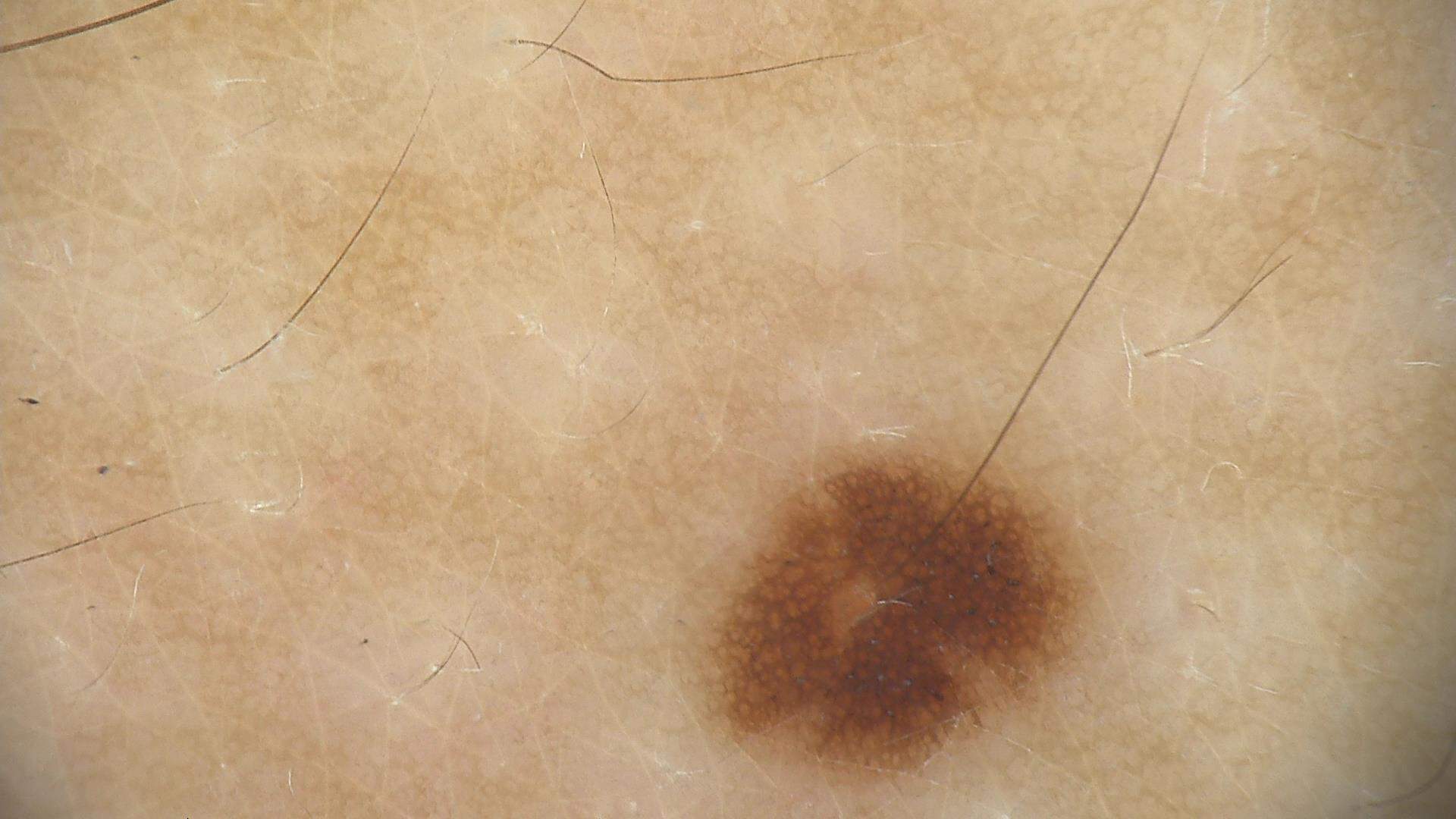<lesion>
<diagnosis>
<name>dysplastic junctional nevus</name>
<code>jd</code>
<malignancy>benign</malignancy>
<super_class>melanocytic</super_class>
<confirmation>expert consensus</confirmation>
</diagnosis>
</lesion>